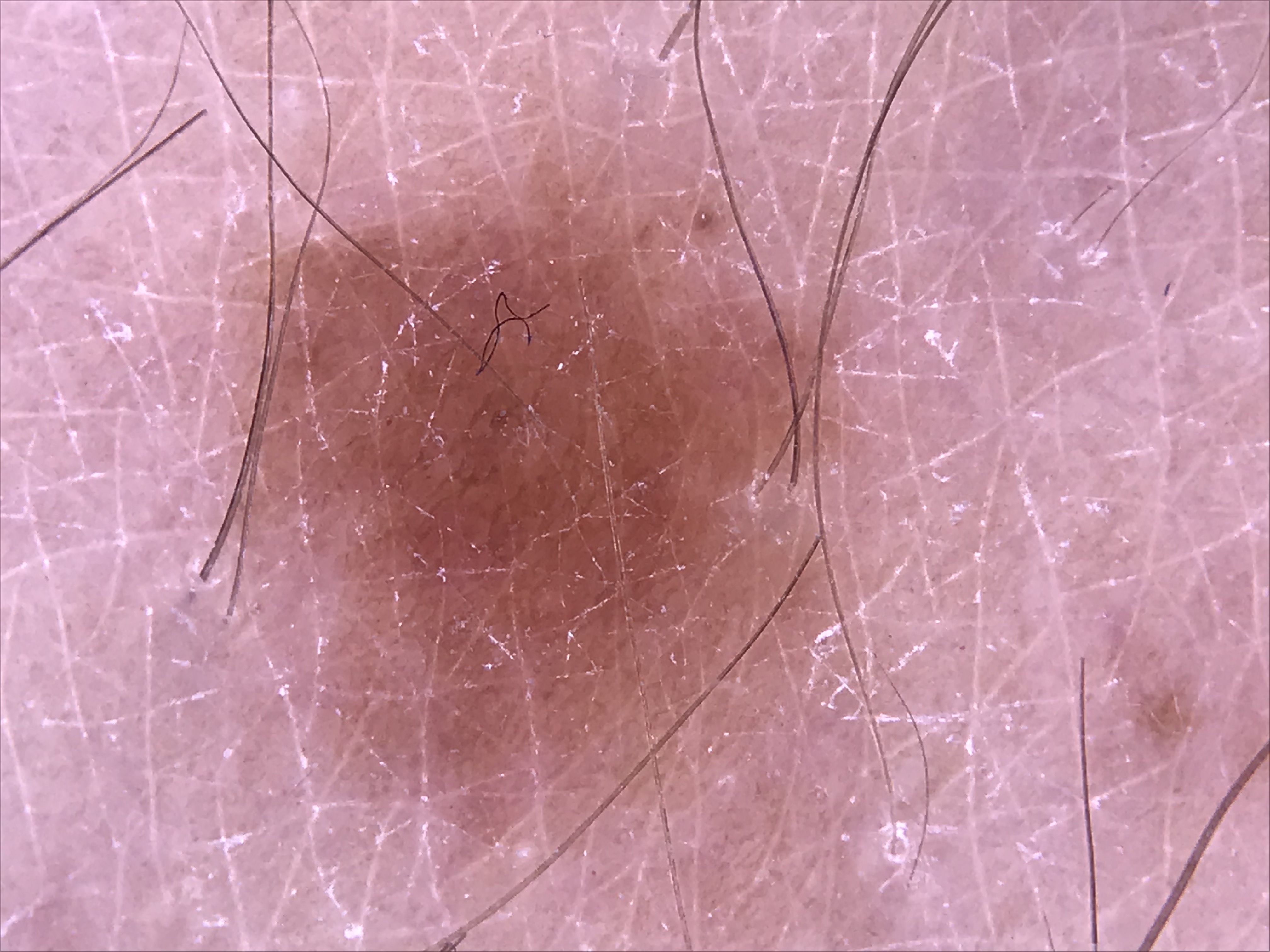<lesion>
  <image>dermoscopy</image>
  <diagnosis>
    <name>junctional nevus</name>
    <code>jb</code>
    <malignancy>benign</malignancy>
    <super_class>melanocytic</super_class>
    <confirmation>expert consensus</confirmation>
  </diagnosis>
</lesion>